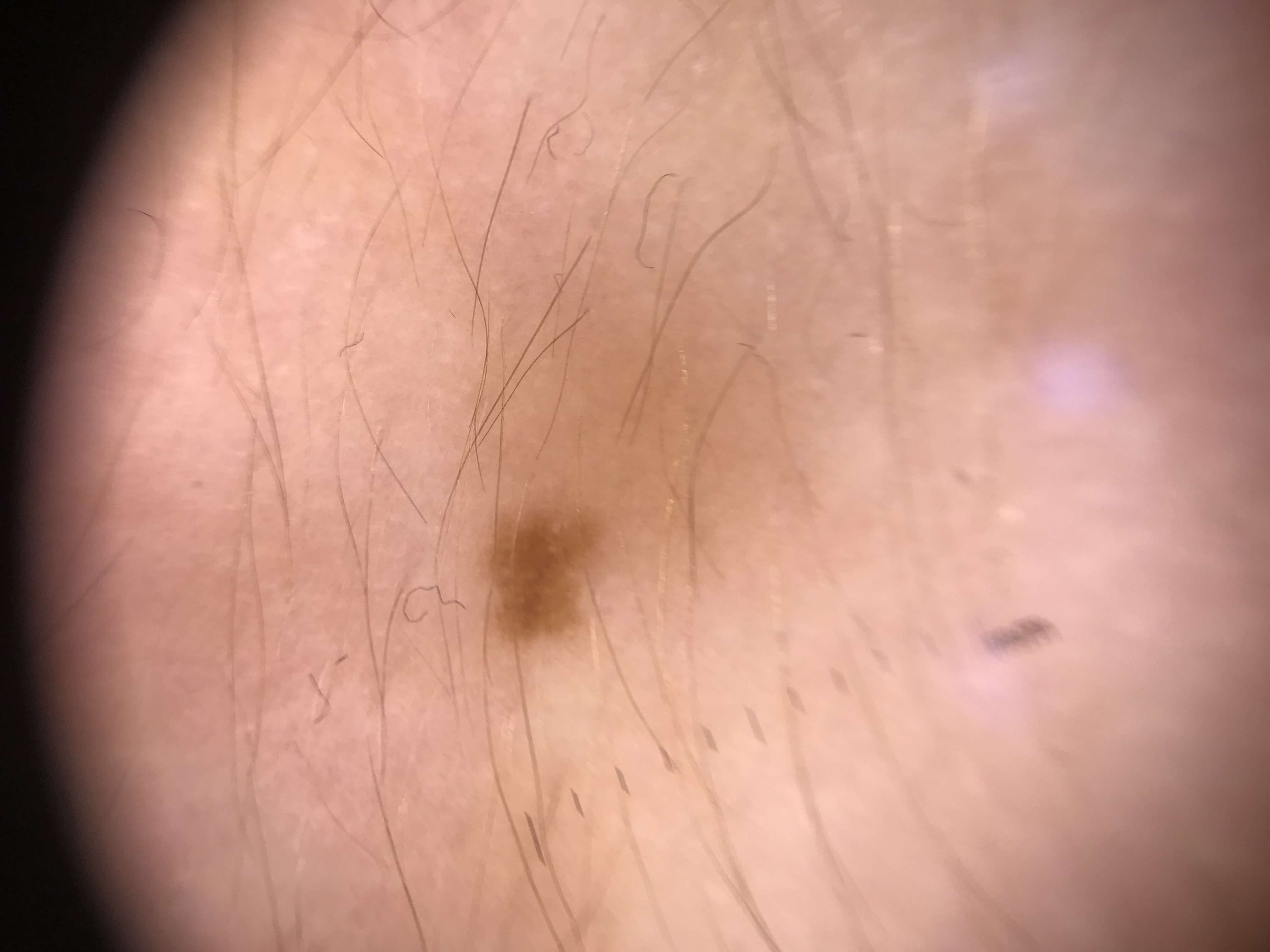Labeled as a junctional nevus.